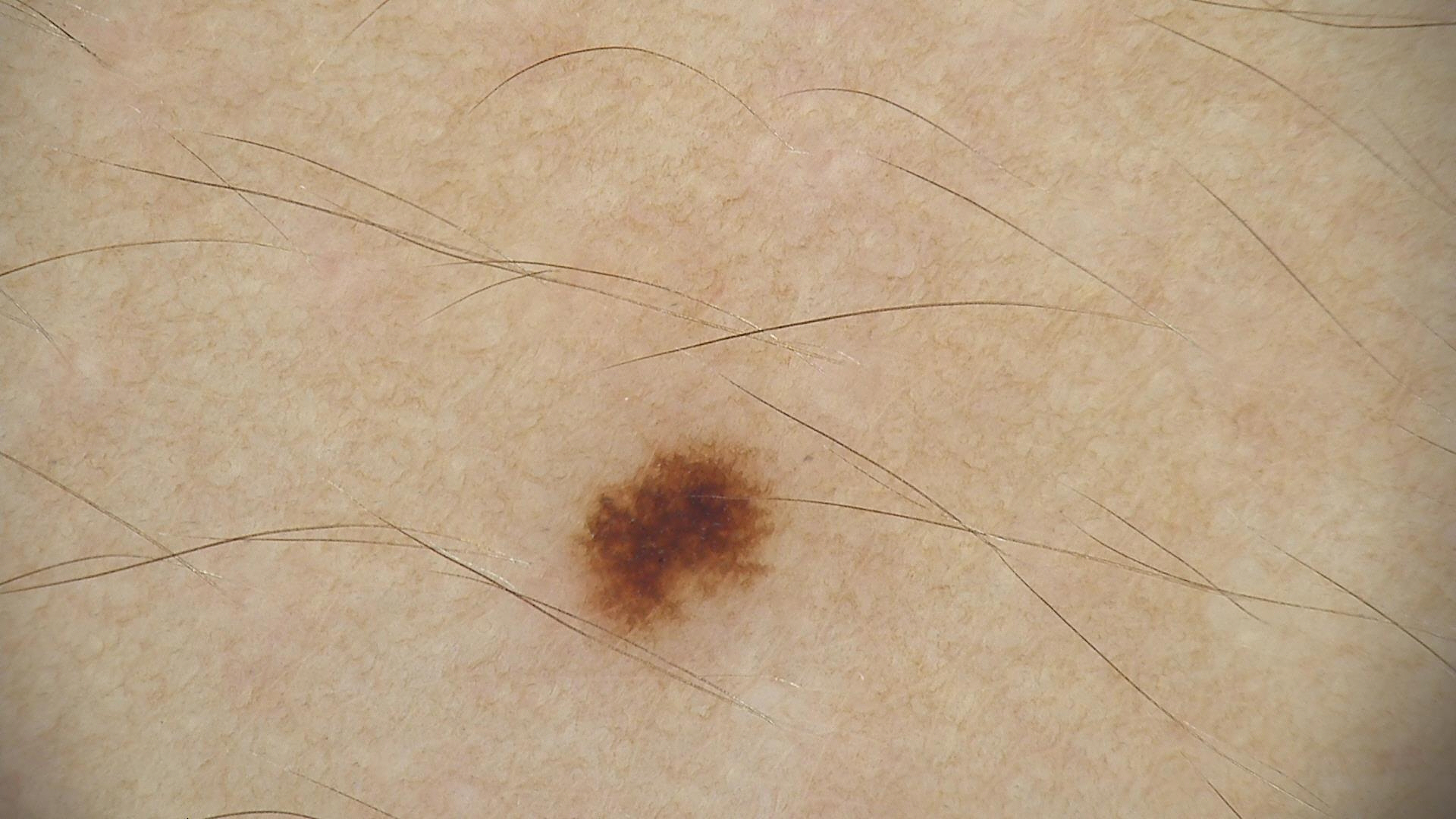A dermoscopic close-up of a skin lesion.
Diagnosed as a dysplastic junctional nevus.